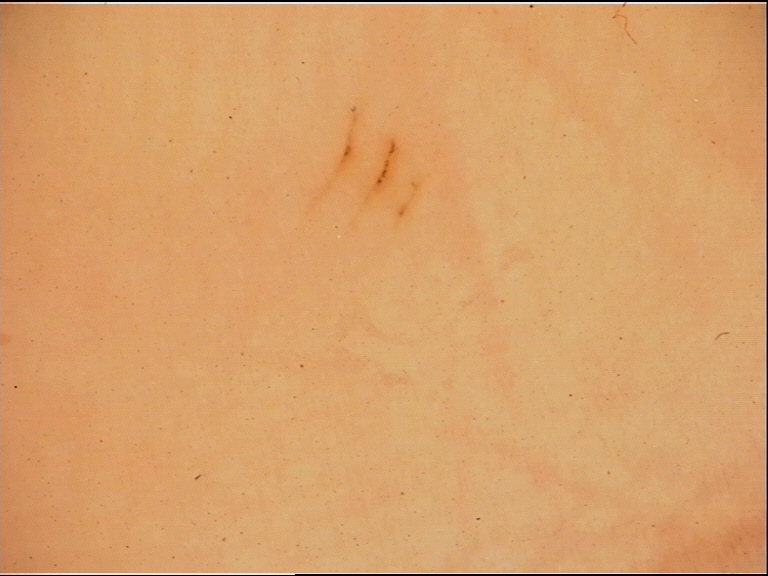Findings:
• diagnostic label — acral junctional nevus (expert consensus)